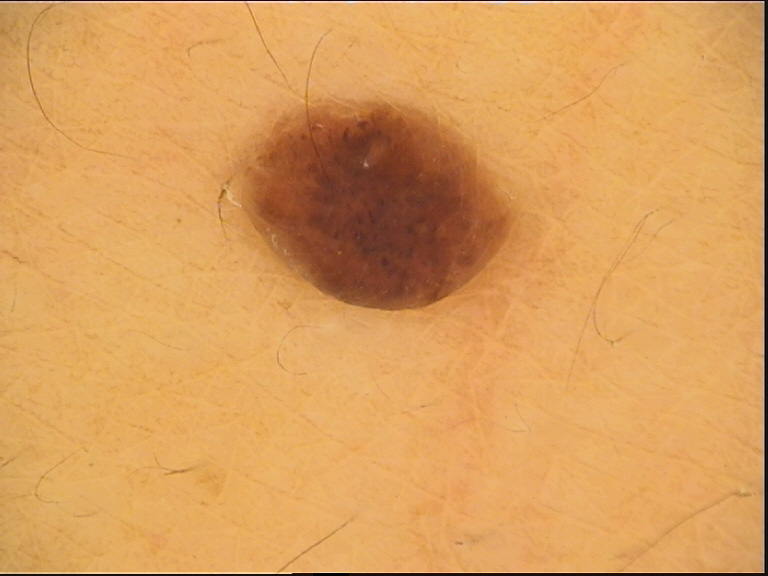lesion_type:
  main_class: banal
  pattern: dermal
diagnosis:
  name: dermal nevus
  code: db
  malignancy: benign
  super_class: melanocytic
  confirmation: expert consensus